A smartphone photograph of a skin lesion — 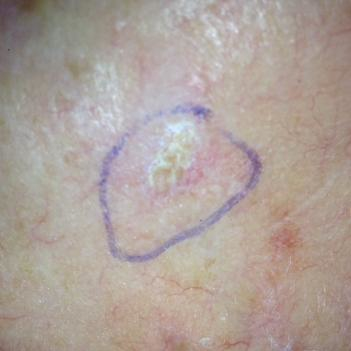Q: What is the anatomic site?
A: the face
Q: Any reported symptoms?
A: itching
Q: What is the diagnosis?
A: actinic keratosis (clinical consensus)